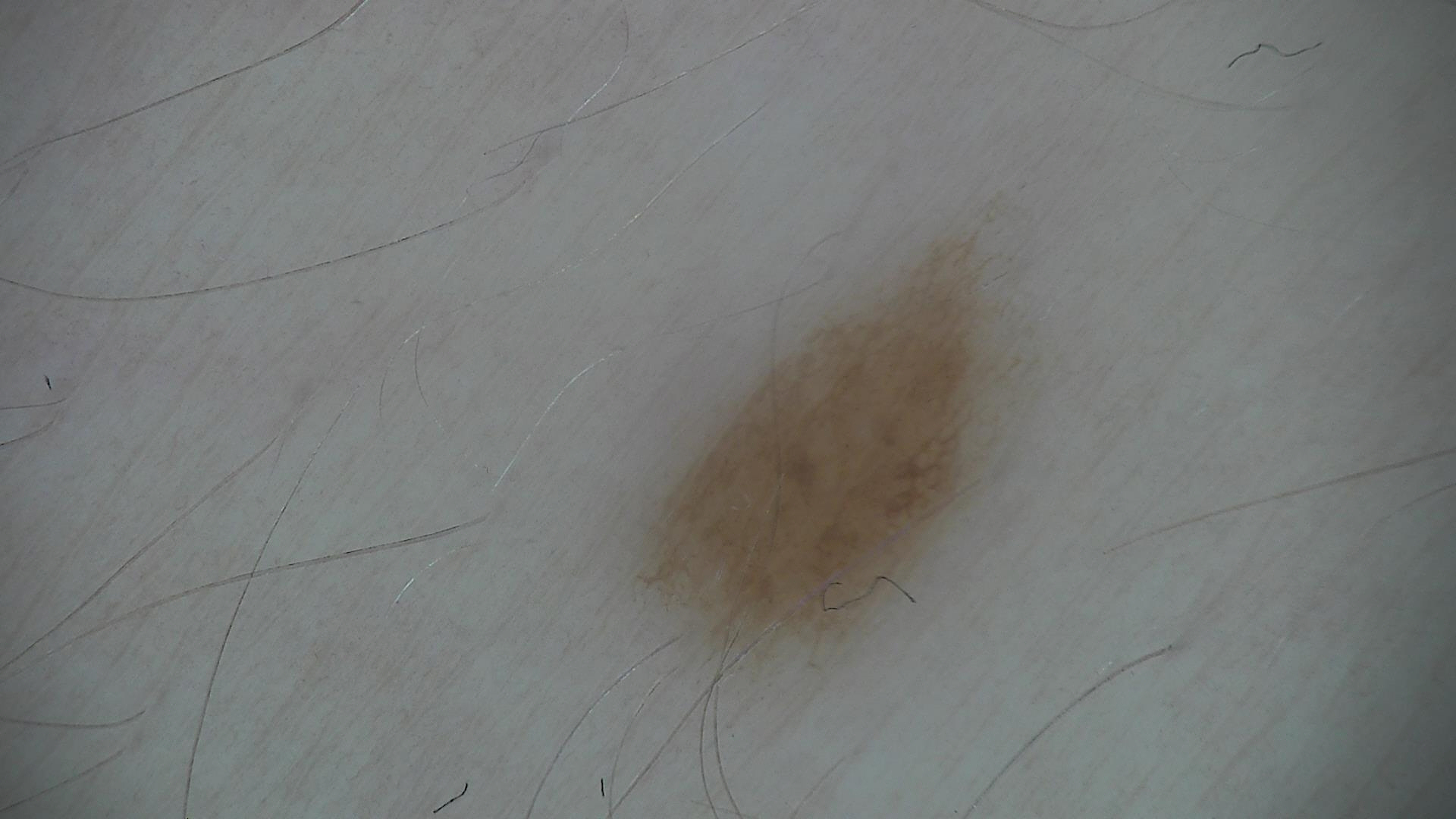Classified as a dysplastic junctional nevus.